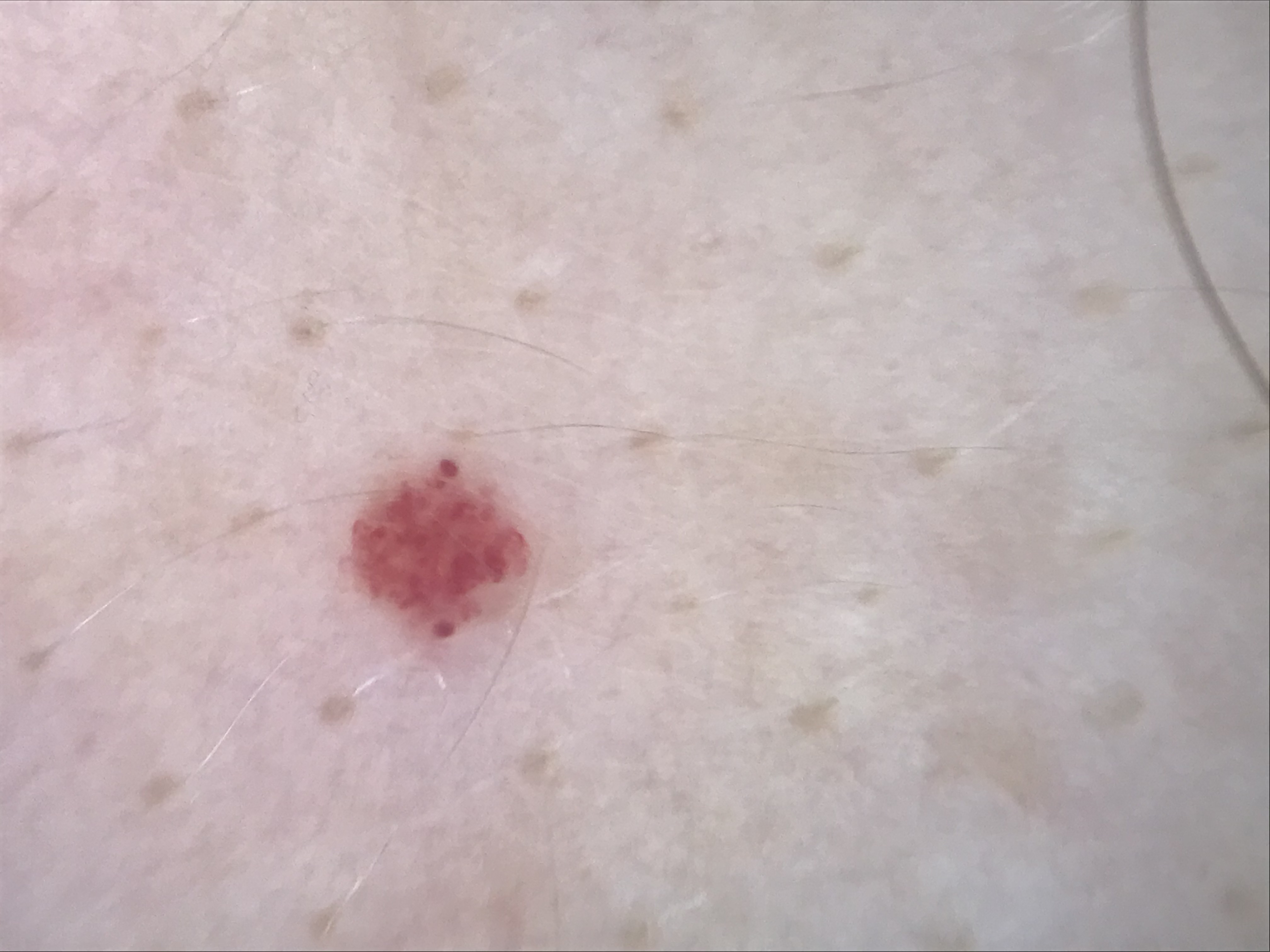Impression: The diagnosis was a hemangioma.